A patient aged 43. A smartphone photograph of a skin lesion:
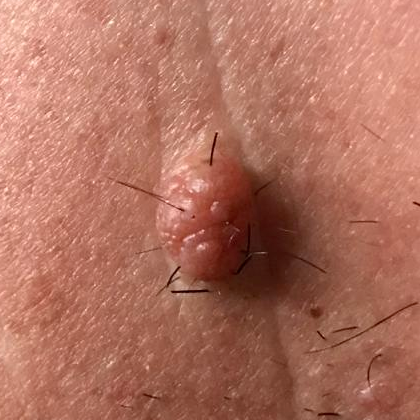The lesion involves the face.
Per patient report, the lesion is elevated and has grown.
The diagnostic impression was a benign lesion — a nevus.